Recorded as skin type I; a clinical photograph showing a skin lesion; by history, prior malignancy (patient or family), no tobacco use, and no pesticide exposure; a female patient in their mid-60s.
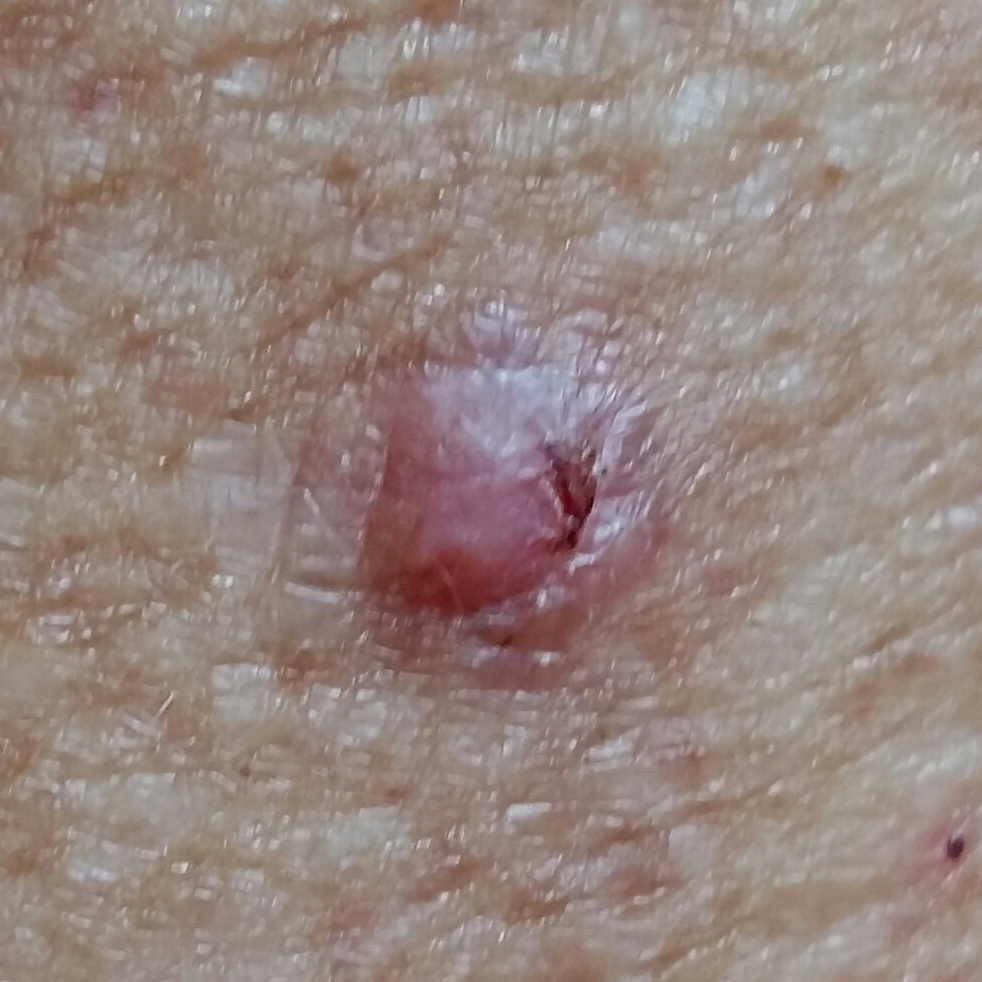Findings:
• location · an arm
• size · 10 × 5 mm
• symptoms · elevation, bleeding, itching
• pathology · basal cell carcinoma (biopsy-proven)